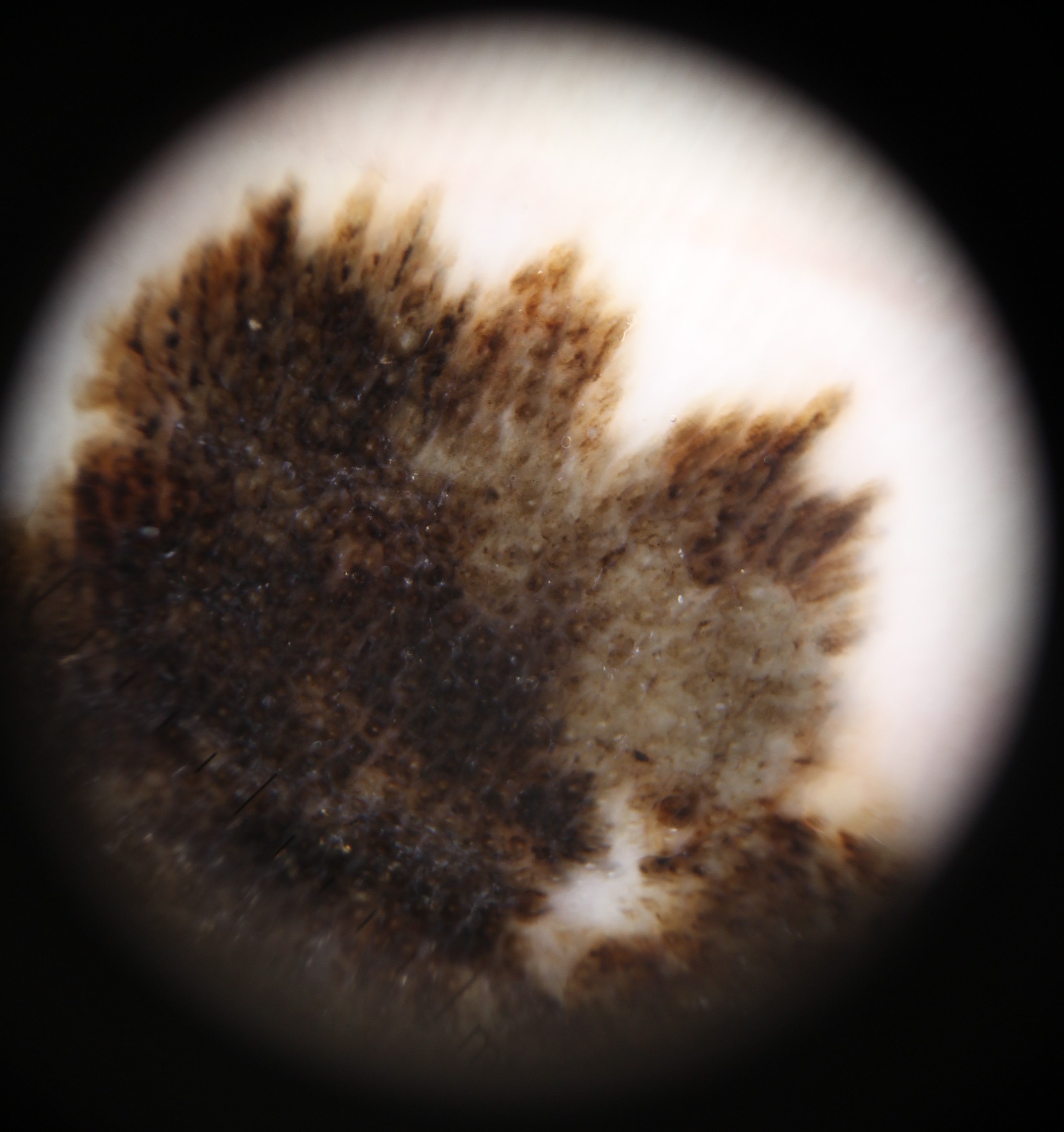Q: What is the diagnosis?
A: acral lentiginous melanoma (biopsy-proven)